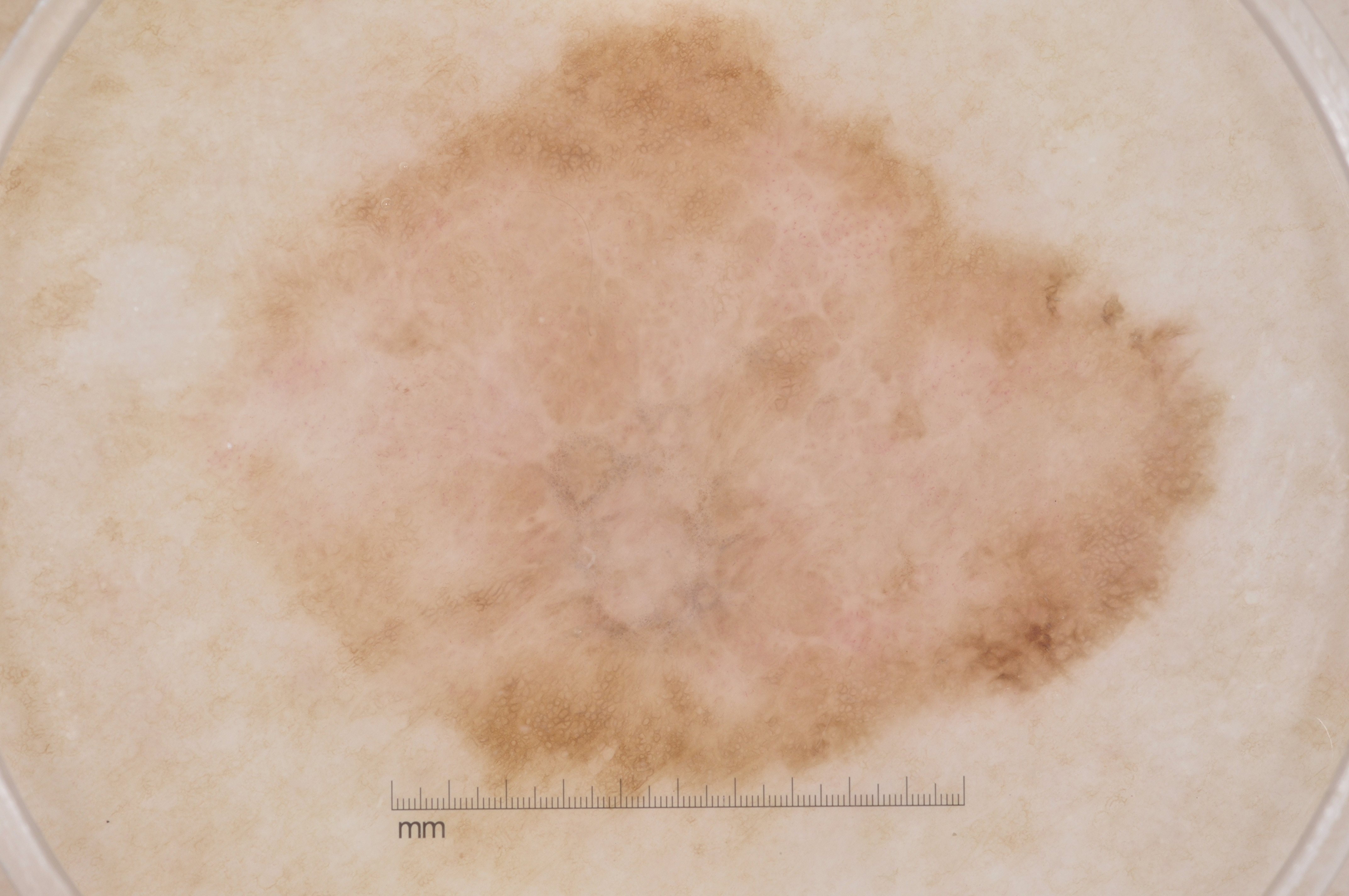This is a dermoscopic photograph of a skin lesion. A female patient in their mid-80s or older. The visible lesion spans left=45, top=1, right=1247, bottom=819. On dermoscopy, the lesion shows pigment network, milia-like cysts, and negative network, with no streaks. The lesion takes up a large portion of the image. The biopsy diagnosis was a melanoma, a malignant skin lesion.